A dermoscopic close-up of a skin lesion.
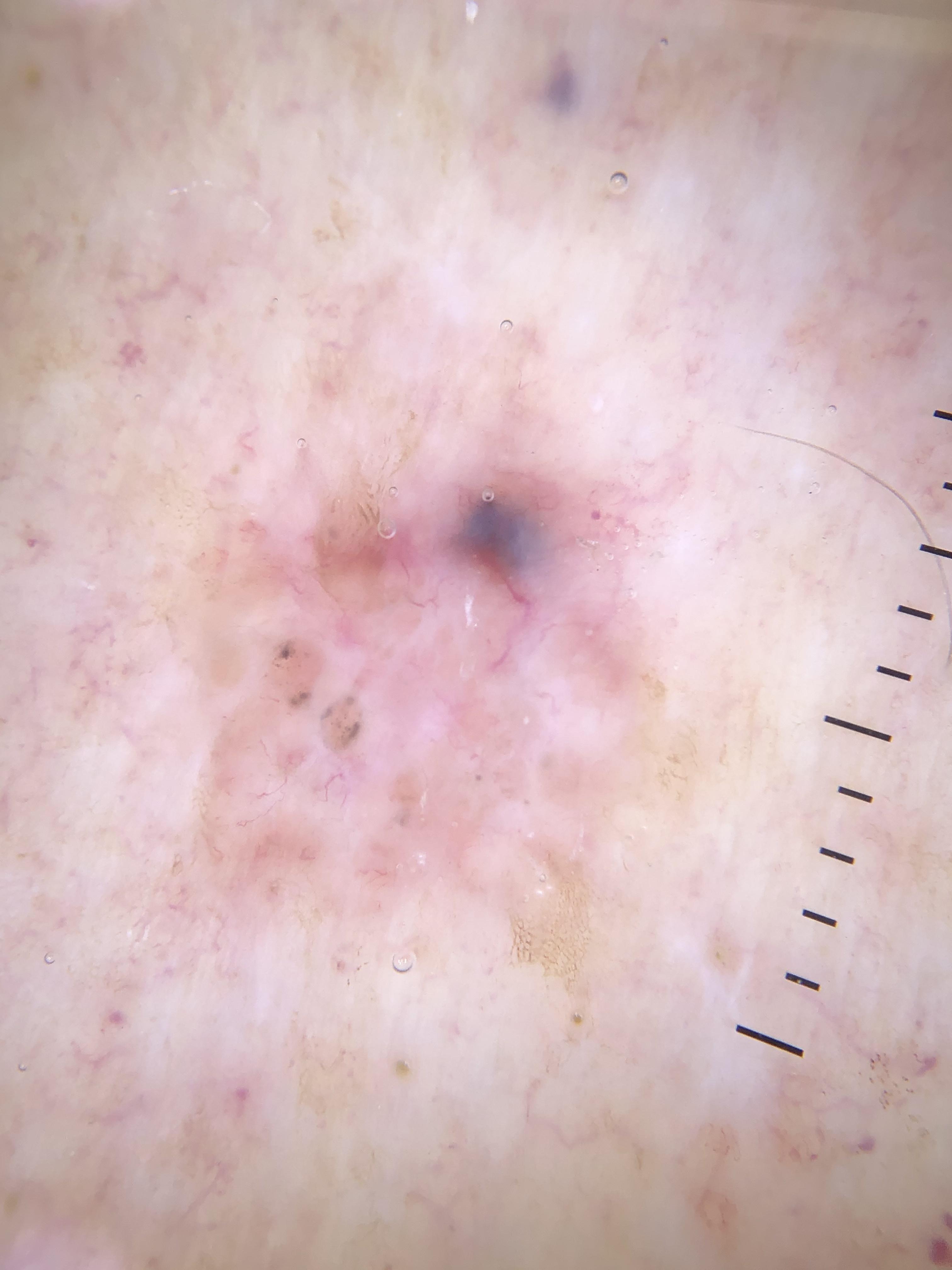The lesion is located on the trunk.
On biopsy, the diagnosis was a malignant, adnexal lesion — a basal cell carcinoma.